A dermoscopic image of a skin lesion: 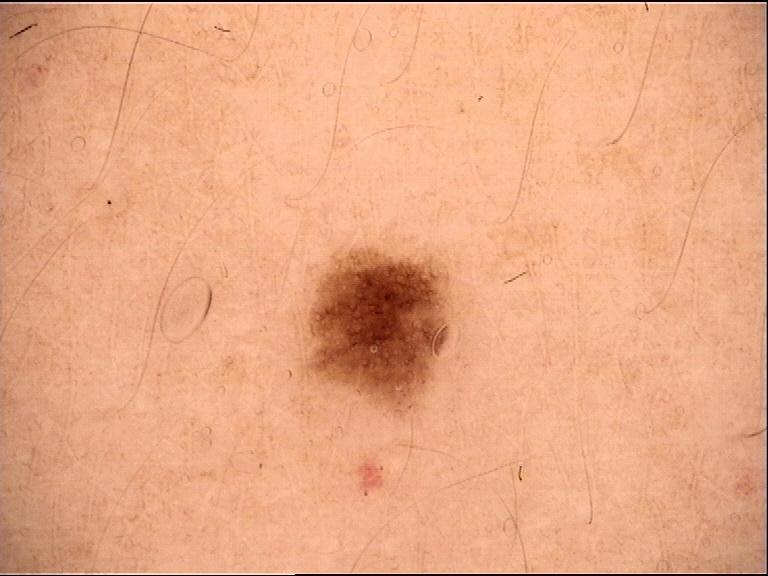Diagnosed as a dysplastic junctional nevus.